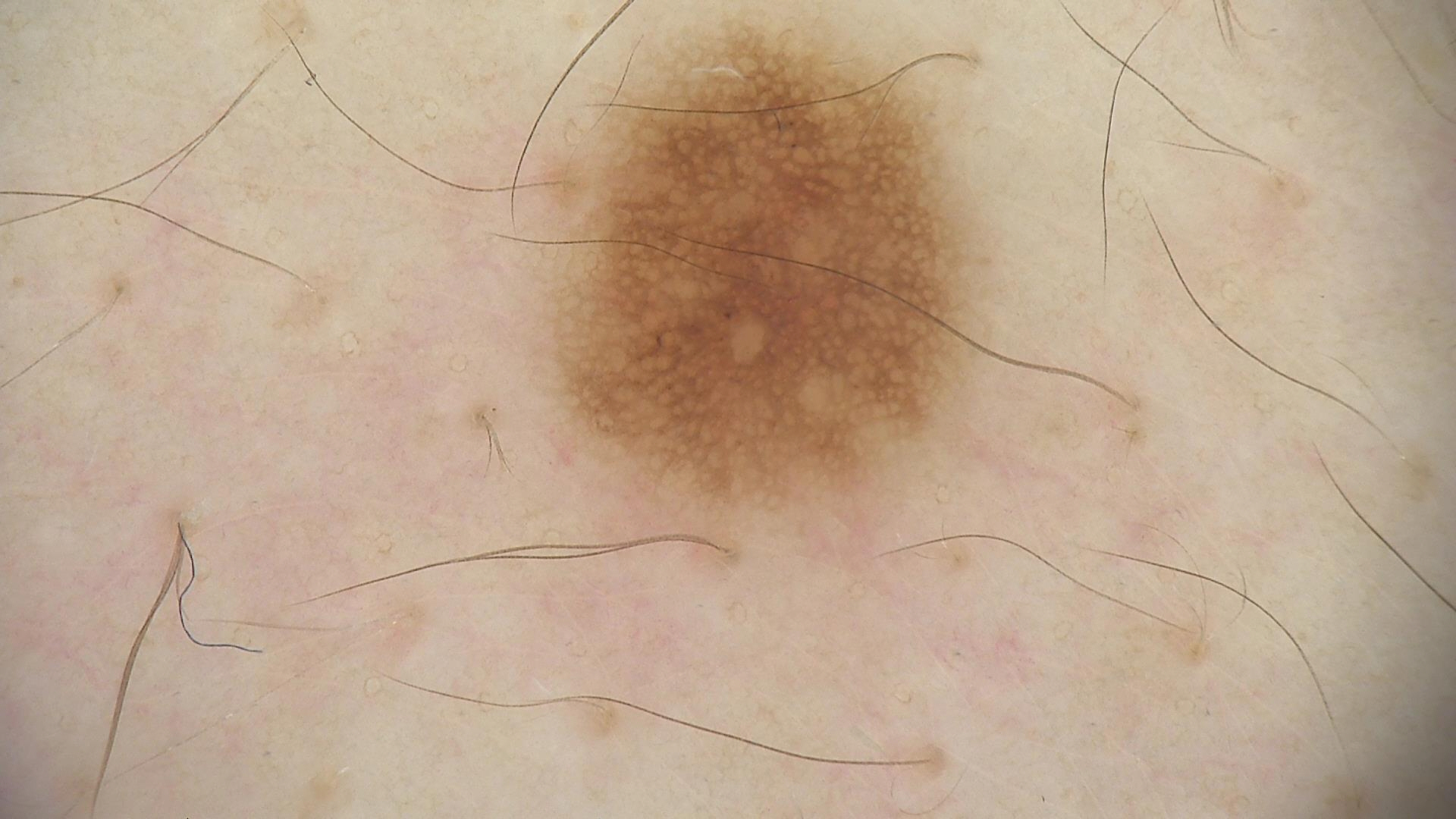imaging = dermoscopy; diagnosis = dysplastic junctional nevus (expert consensus).